The lesion involves the arm · present for one to four weeks · the lesion is described as flat · the patient considered this a rash · the photo was captured at an angle · the contributor notes itching and enlargement.
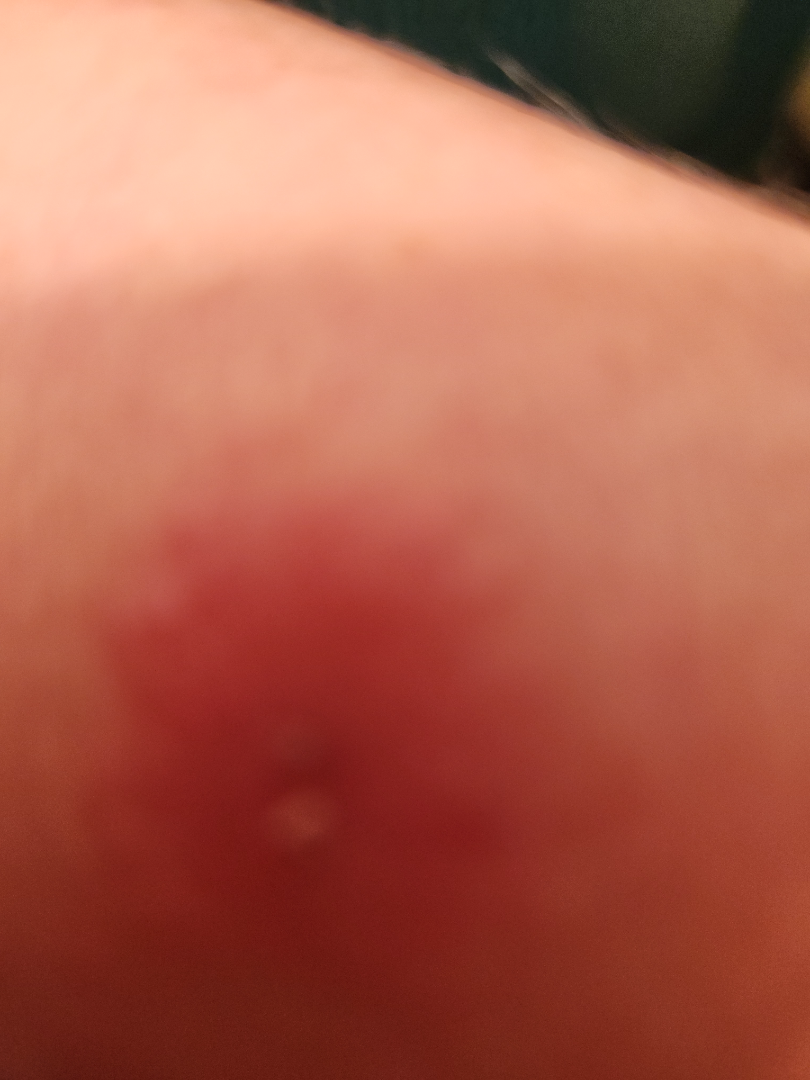No differential diagnosis could be assigned on photographic review.